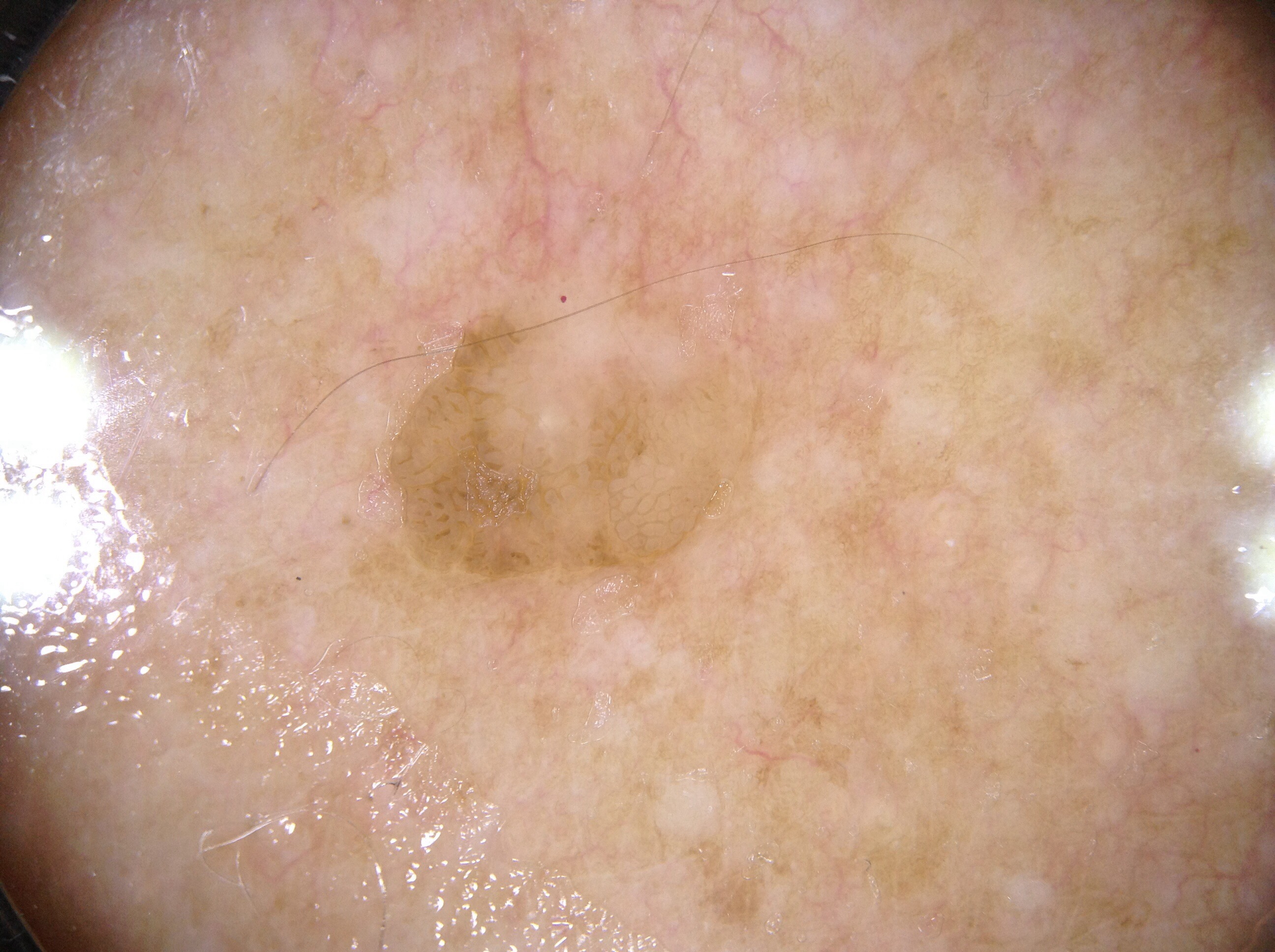Notes:
- patient — male, aged around 60
- image type — dermoscopy of a skin lesion
- dermoscopic findings — pigment network
- bounding box — <bbox>378, 237, 771, 610</bbox>
- assessment — a seborrheic keratosis, a benign skin lesion